The photograph is a close-up of the affected area; the patient is a male aged 50–59.
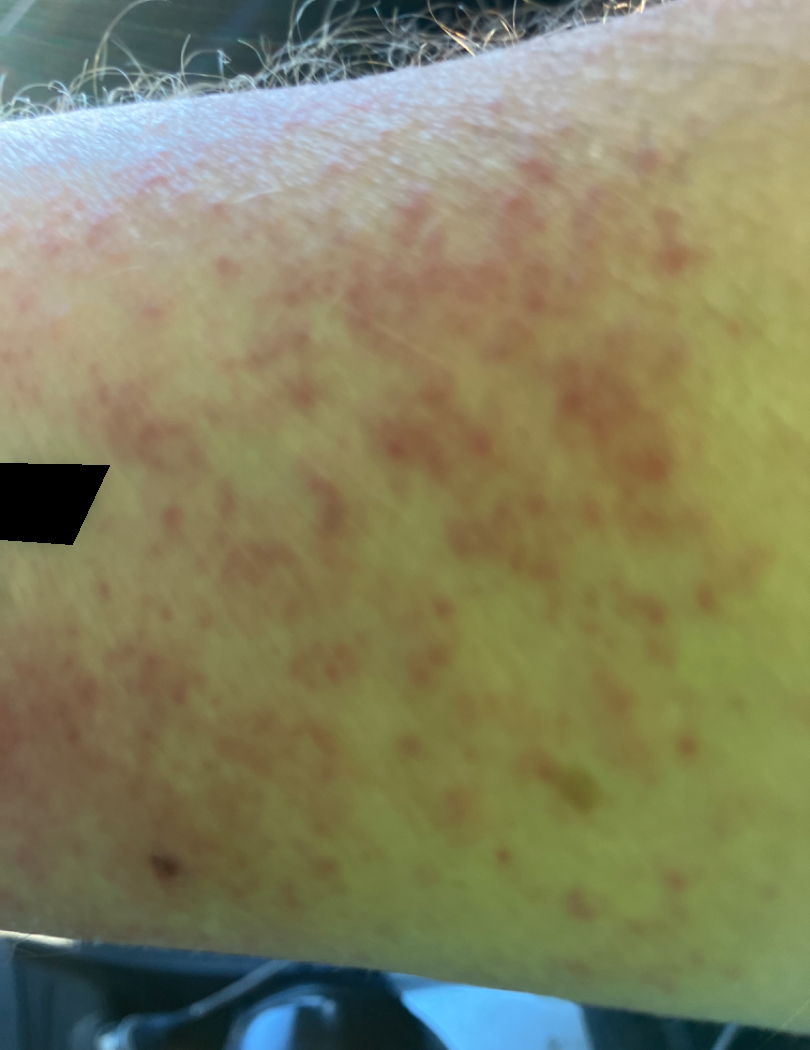assessment = could not be assessed.